A contact-polarized dermoscopy image of a skin lesion:
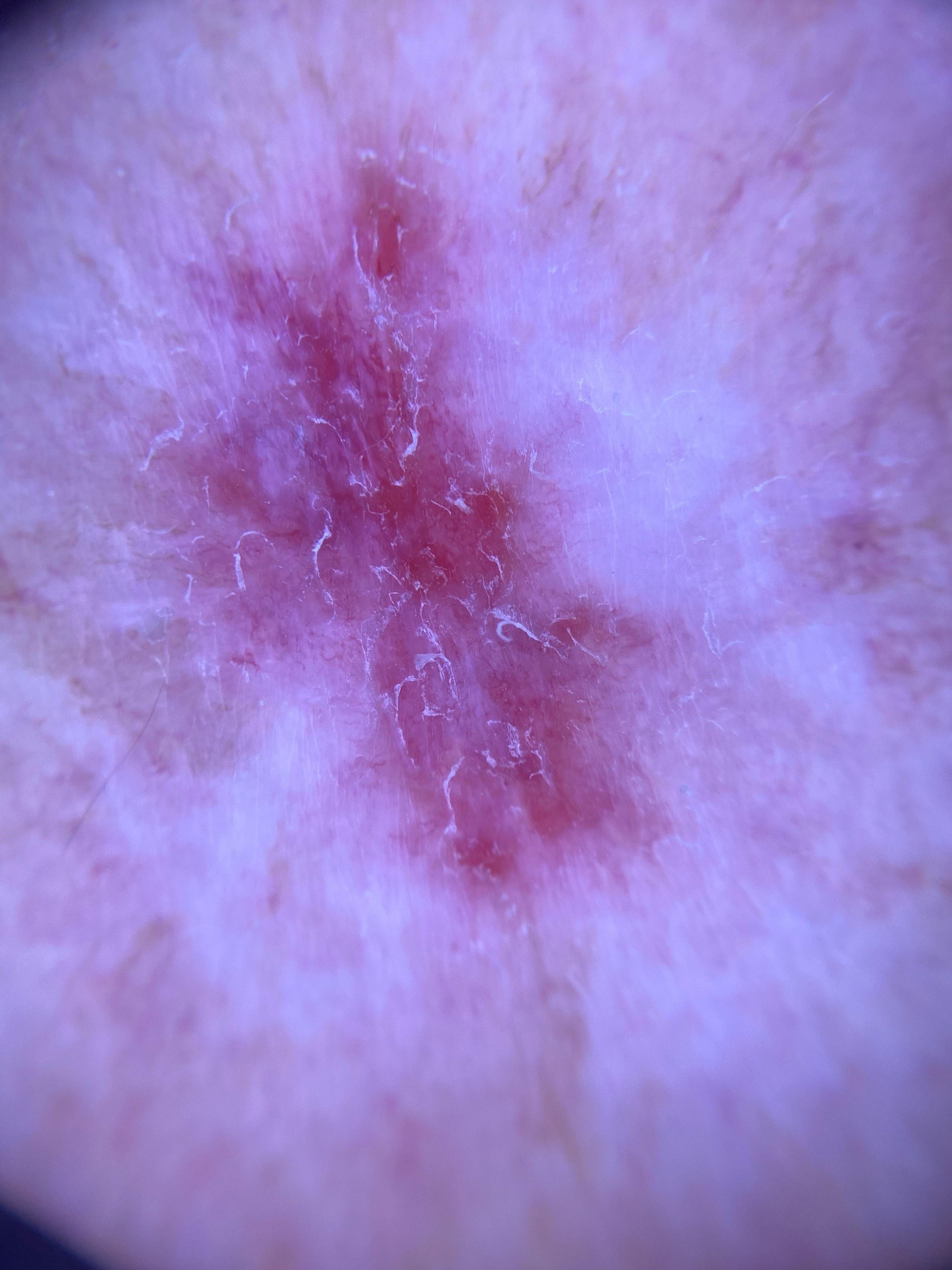The lesion was found on the anterior trunk. Confirmed on histopathology as a basal cell carcinoma.